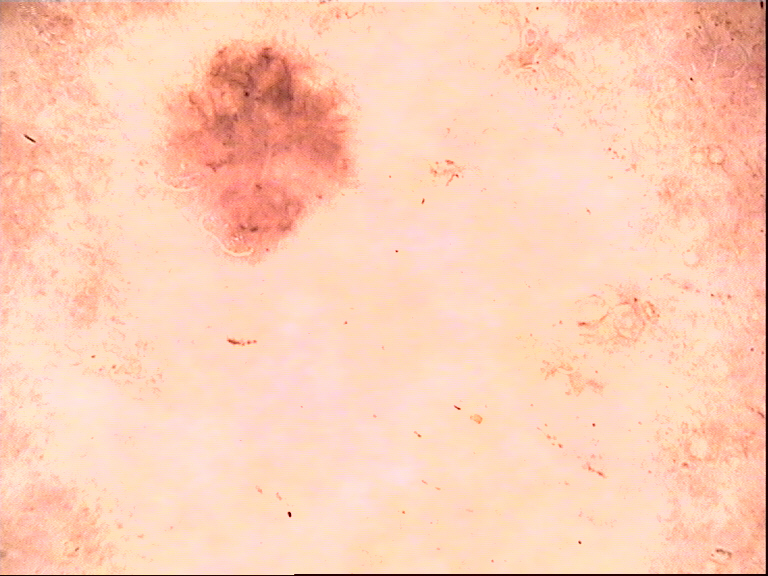A dermoscopic image of a skin lesion. The diagnostic label was a benign lesion — a dysplastic compound nevus.